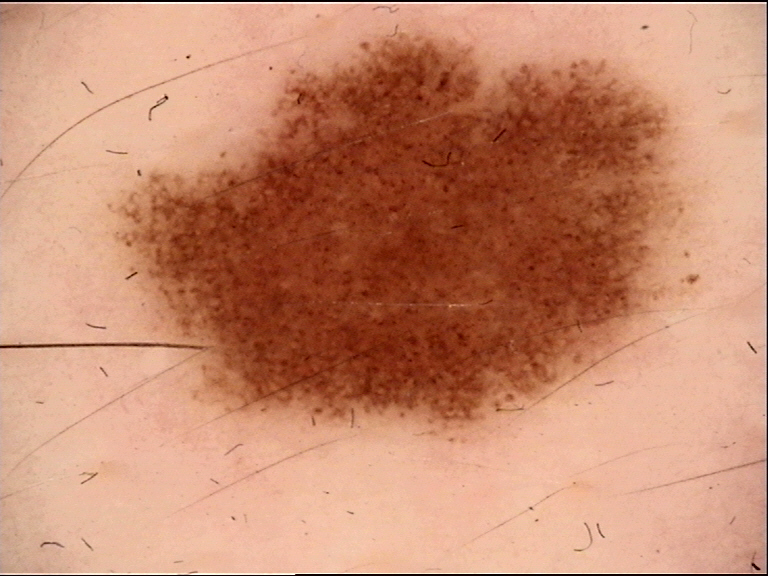A dermoscopy image of a single skin lesion. Labeled as a dysplastic junctional nevus.